A dermoscopy image of a single skin lesion:
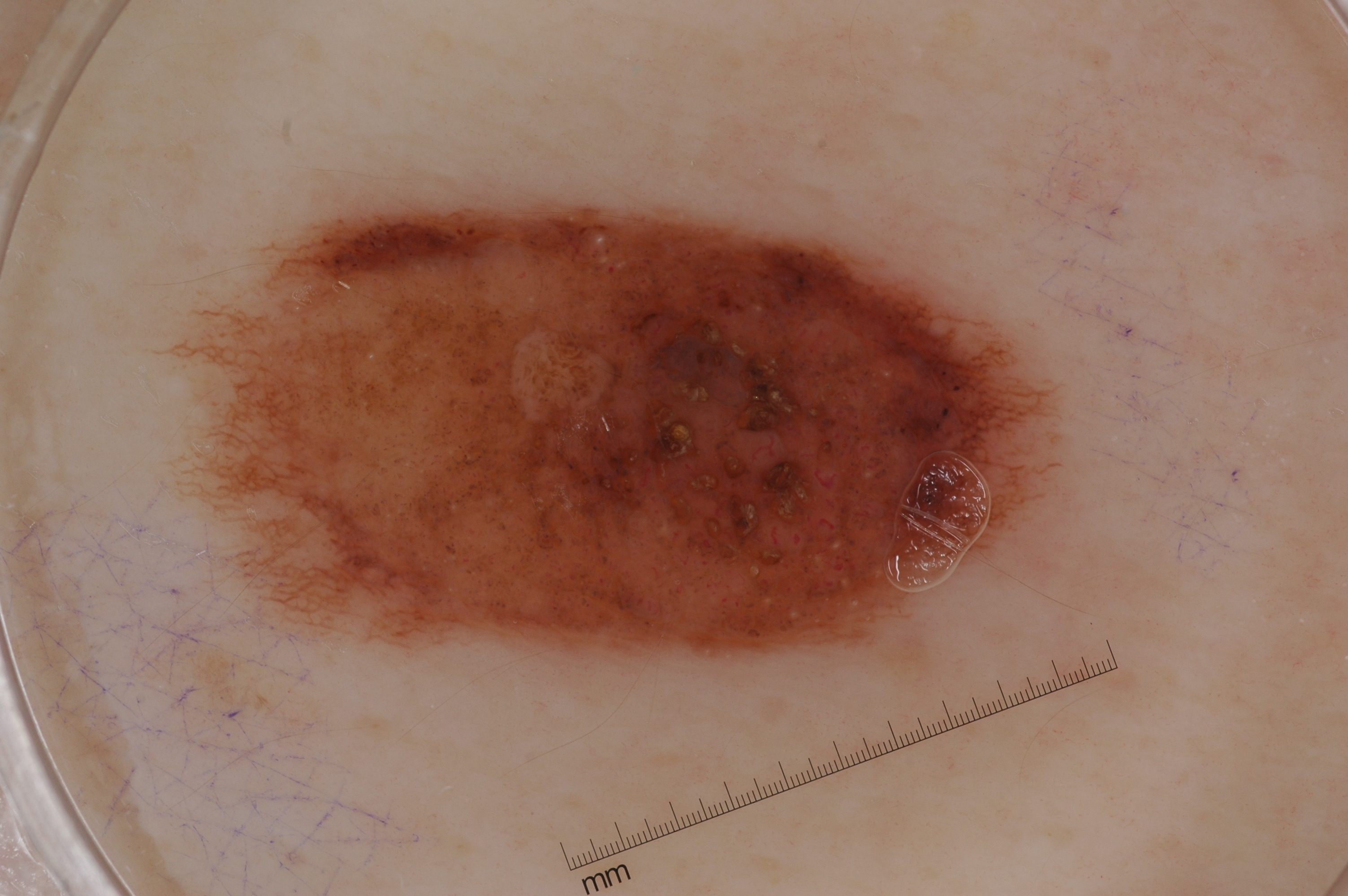As (left, top, right, bottom), the lesion's extent is 190, 203, 1053, 658. Dermoscopic review identifies pigment network and milia-like cysts; no negative network or streaks. A moderately sized lesion. Diagnosed as a melanocytic nevus, a benign lesion.